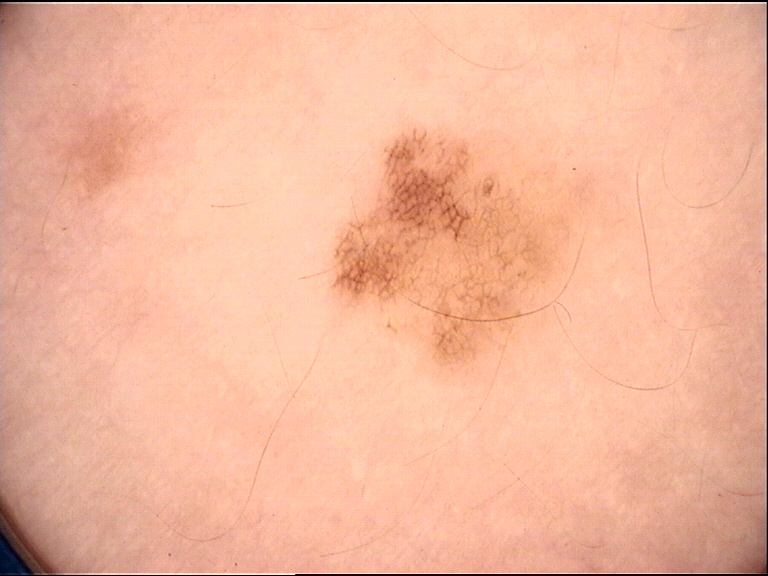Summary: A dermoscopic photograph of a skin lesion. Impression: Labeled as a banal lesion — a congenital junctional nevus.